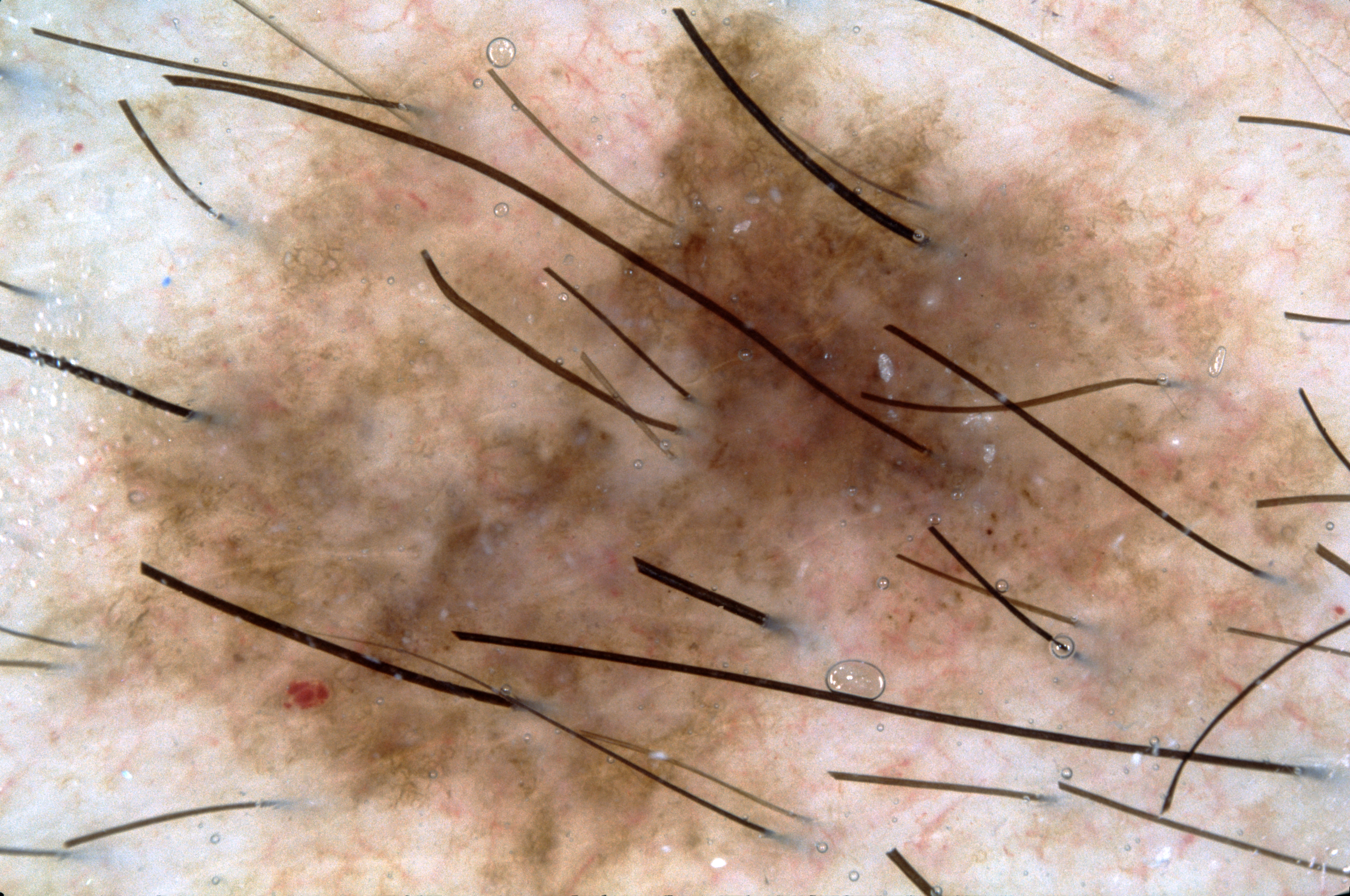image type = dermoscopy
lesion location = reaches across the whole image
dermoscopic features = pigment network and milia-like cysts; absent: negative network and streaks
diagnosis = a melanoma